Located on the arm · the lesion is described as raised or bumpy · reported duration is about one day · female subject, age 30–39 · the patient considered this a rash · no relevant systemic symptoms · a close-up photograph — 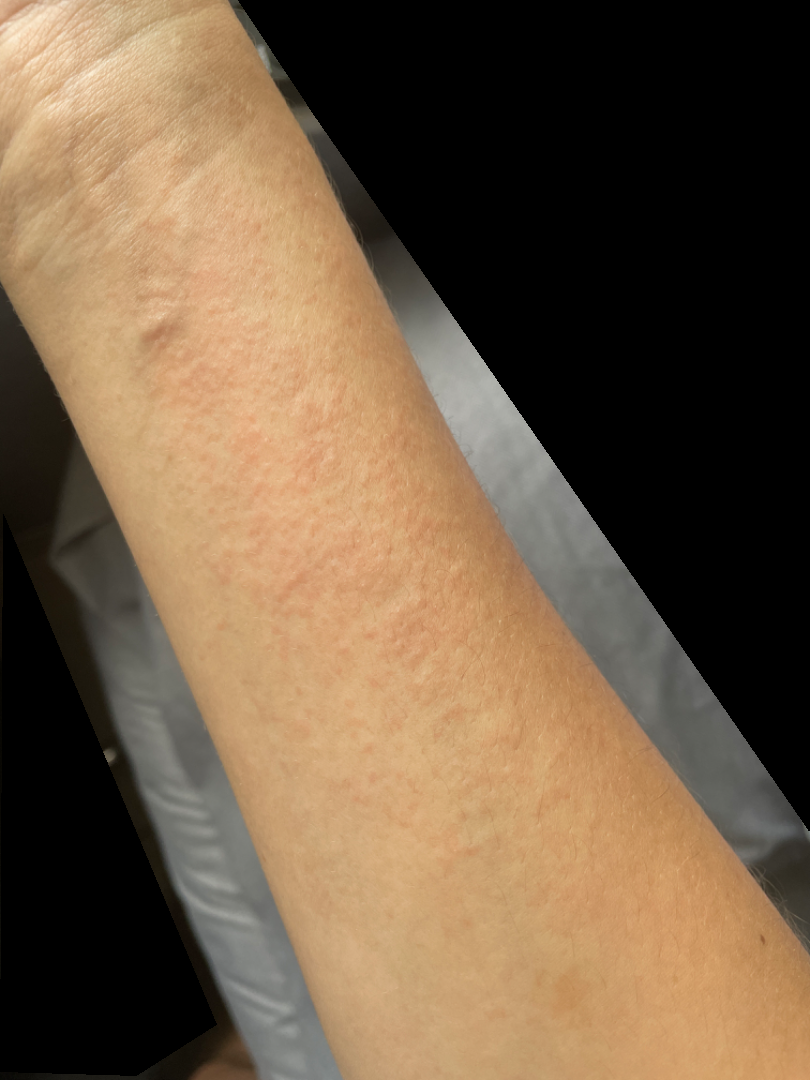Findings:
- impression: most consistent with Eczema